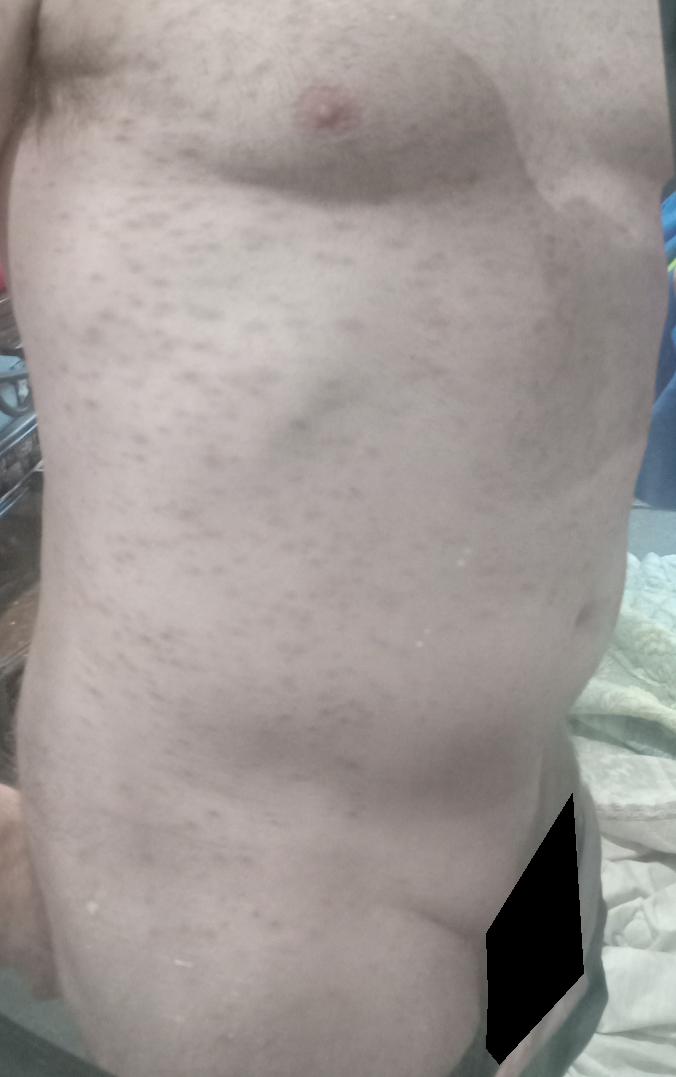Clinical context: The photo was captured at a distance.